A male subject aged around 45, a dermatoscopic image of a skin lesion:
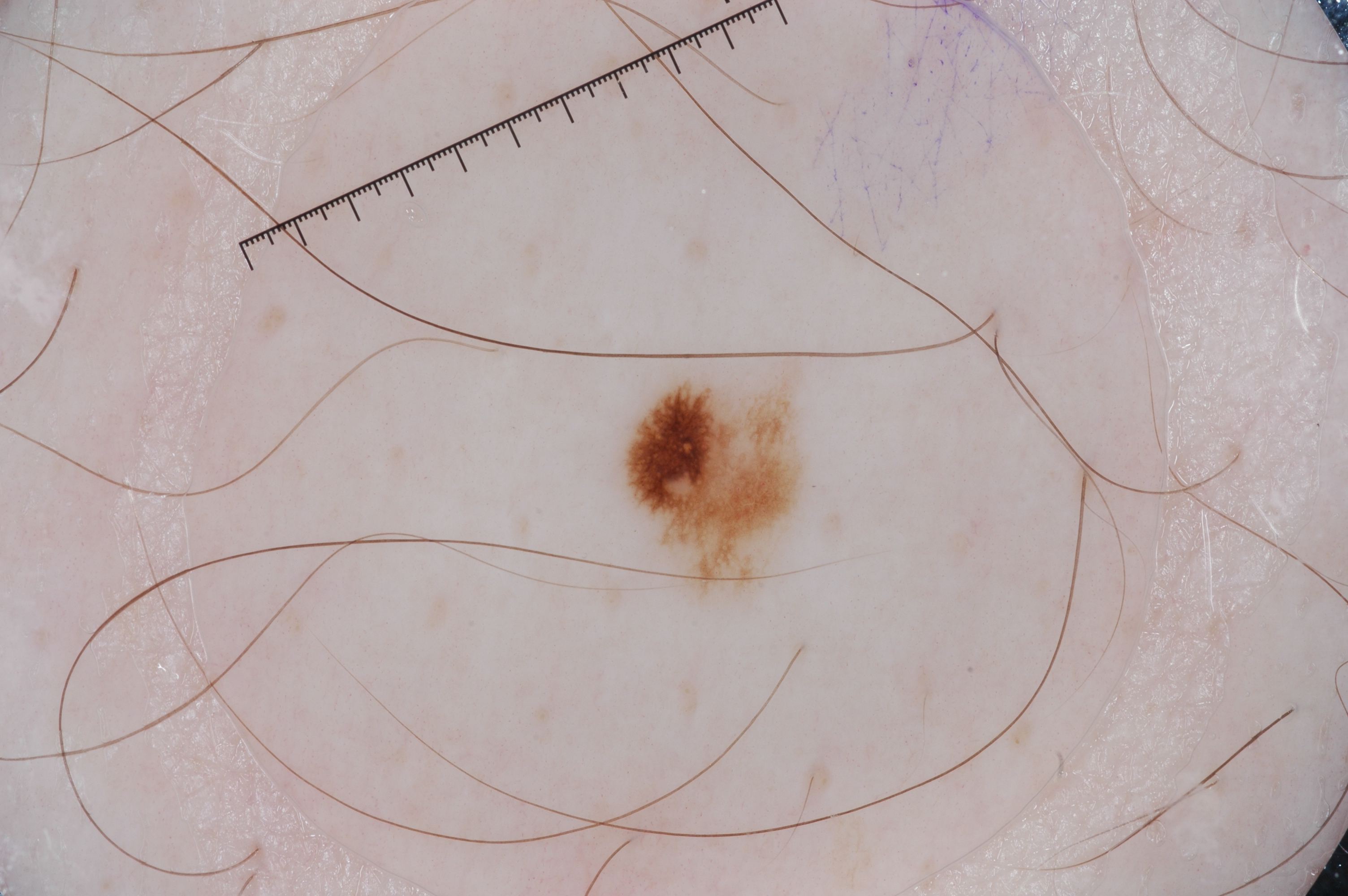| field | value |
|---|---|
| dermoscopic pattern | pigment network; absent: negative network, milia-like cysts, and streaks |
| bounding box | 633 392 801 588 |
| size | small |
| assessment | a melanoma |